A dermatoscopic image of a skin lesion.
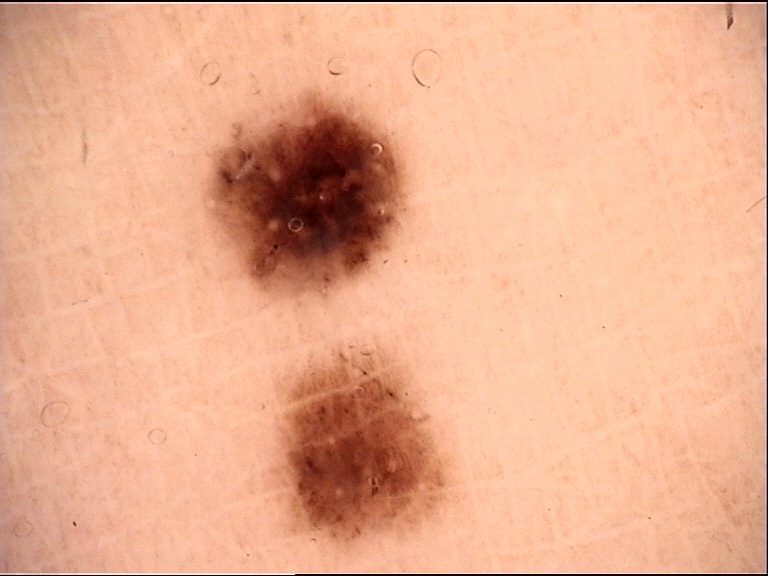class = dysplastic junctional nevus (expert consensus).